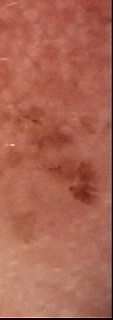image: dermoscopy
class: basal cell carcinoma (biopsy-proven)